Located on the back of the hand. This image was taken at a distance: 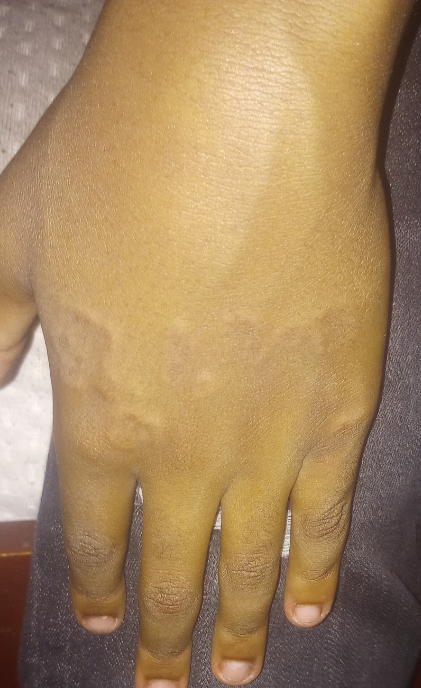Q: What was the assessment?
A: indeterminate
Q: How does the lesion feel?
A: raised or bumpy
Q: Reported symptoms?
A: bothersome appearance
Q: When did this start?
A: one to four weeks
Q: Fitzpatrick or Monk tone?
A: human graders estimated MST 5 (US pool) or 4 (India pool)
Q: Patient's own categorization?
A: a pigmentary problem